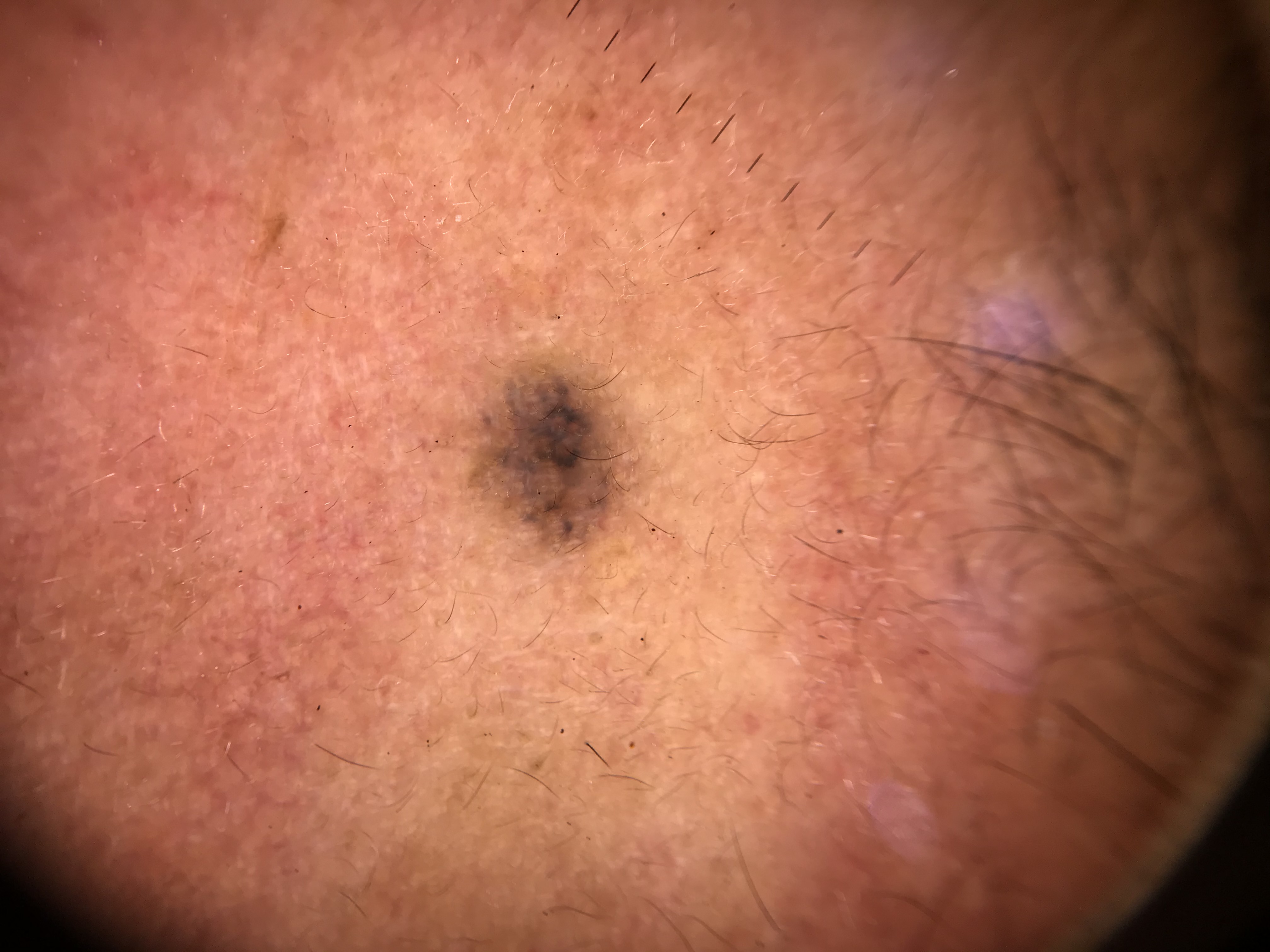Diagnosis: Histopathologically confirmed as a basal cell carcinoma.